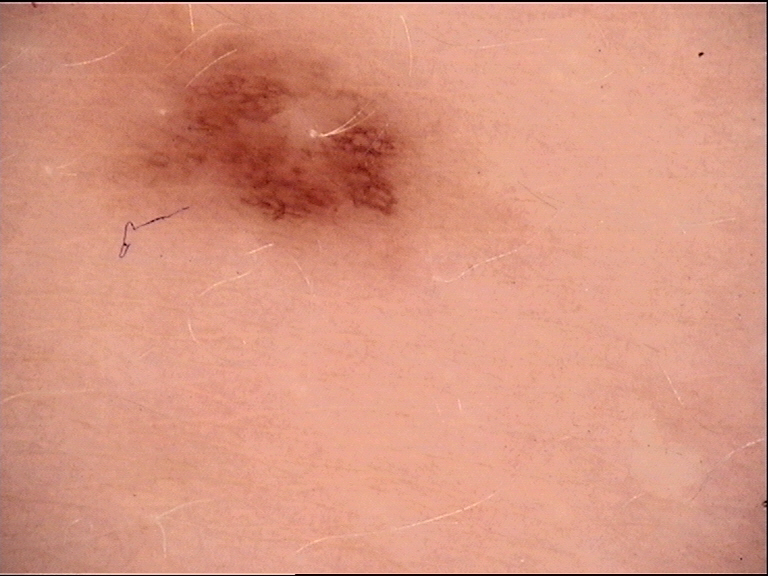Q: What is the imaging modality?
A: dermoscopy
Q: What is this lesion?
A: dysplastic junctional nevus (expert consensus)